A skin lesion imaged with a dermatoscope.
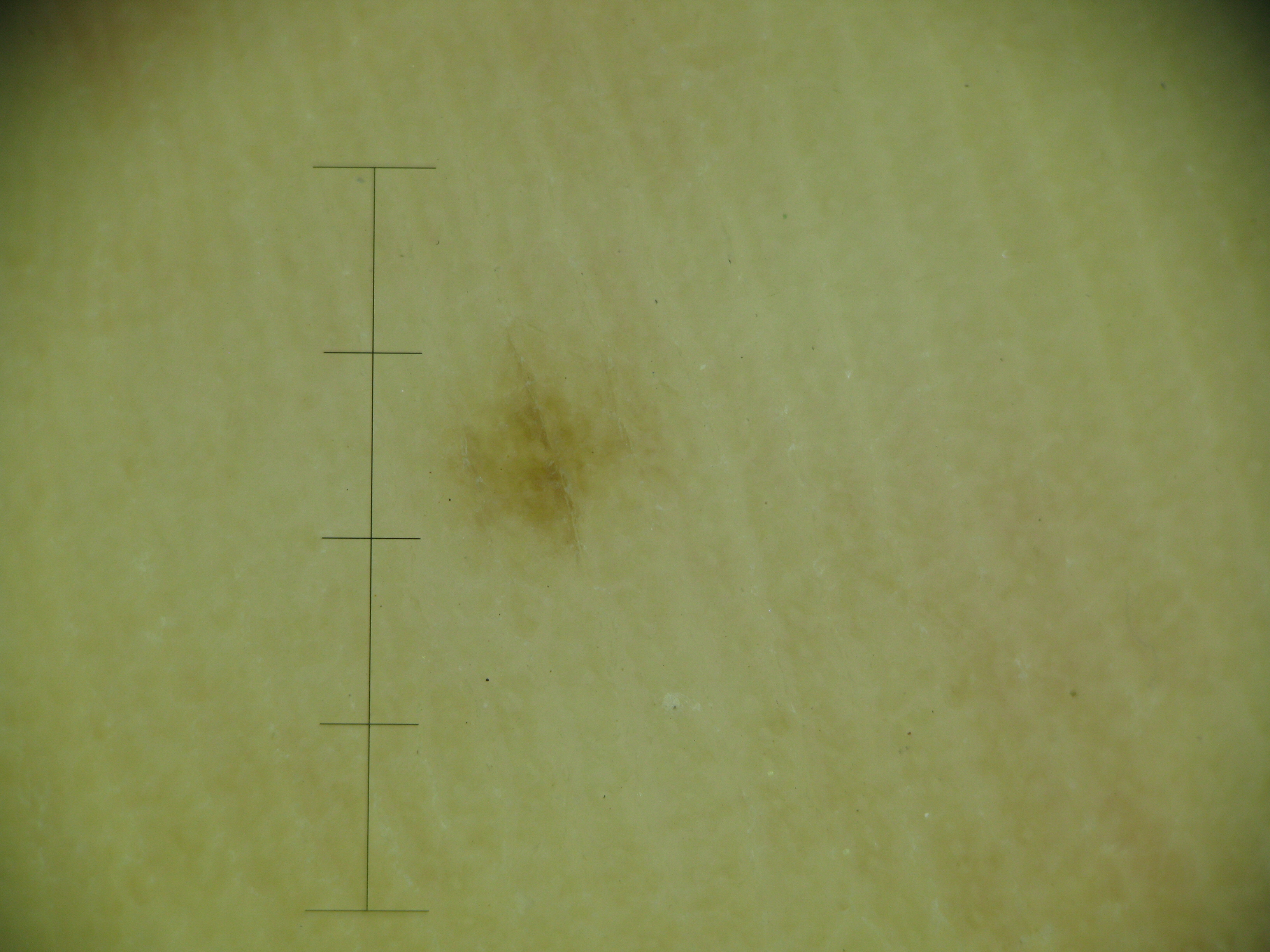Findings:
• classification — banal
• class — acral junctional nevus (expert consensus)